A patient in their late 40s: 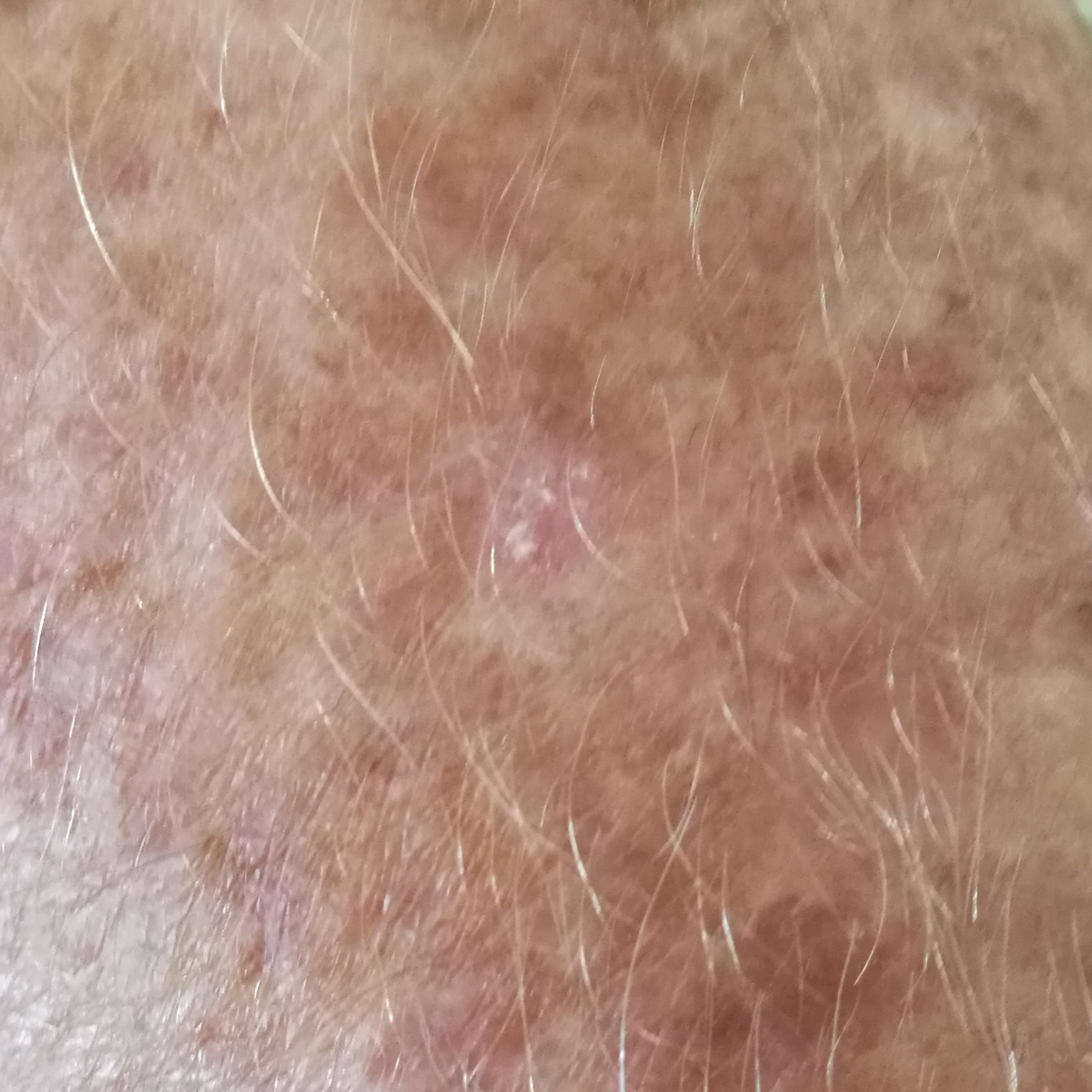The lesion involves a forearm. The consensus clinical diagnosis was an actinic keratosis.